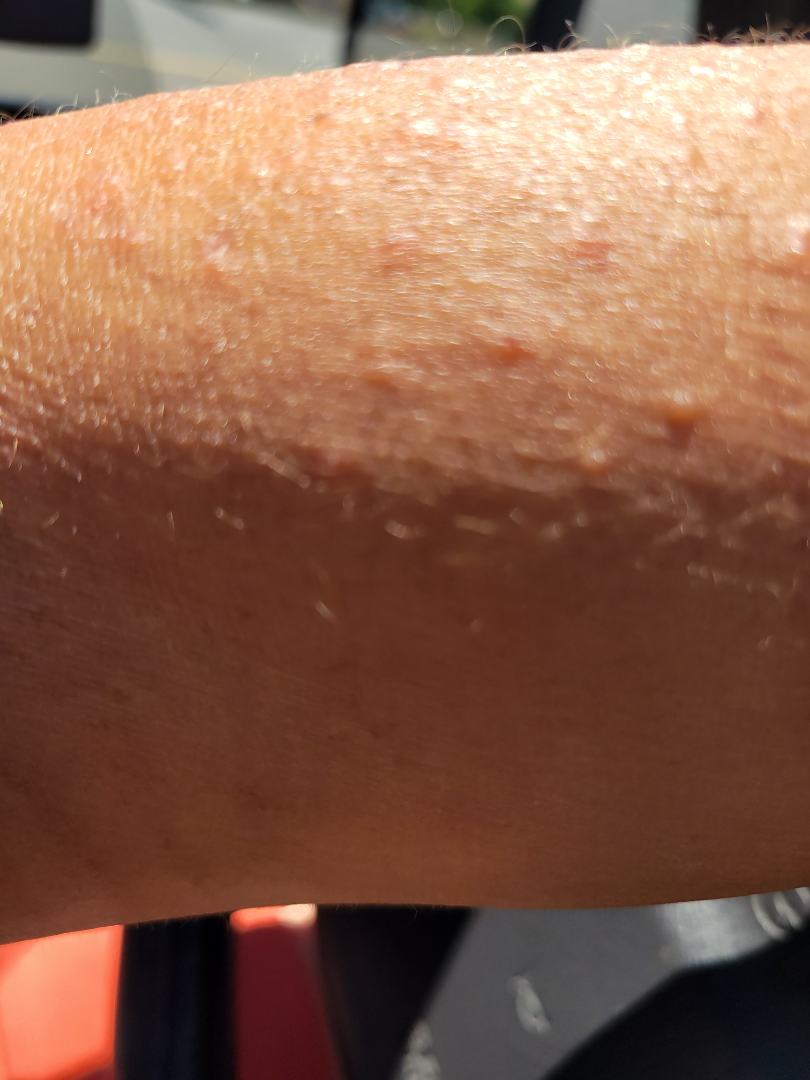The reviewer was unable to grade this case for skin condition. The patient reports itching. An image taken at an angle. The lesion is described as raised or bumpy and fluid-filled. The lesion involves the arm.